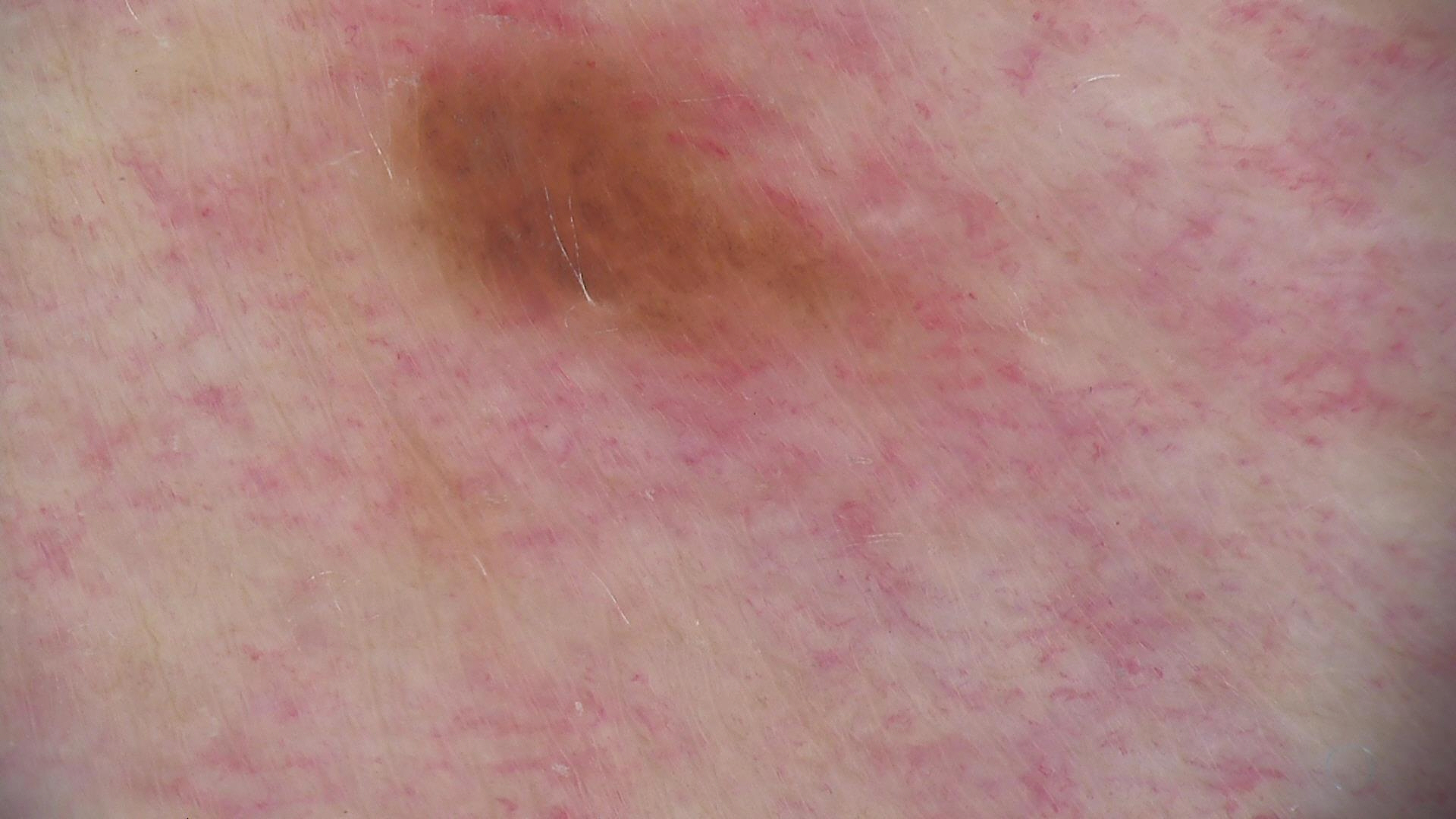Consistent with a dysplastic junctional nevus.